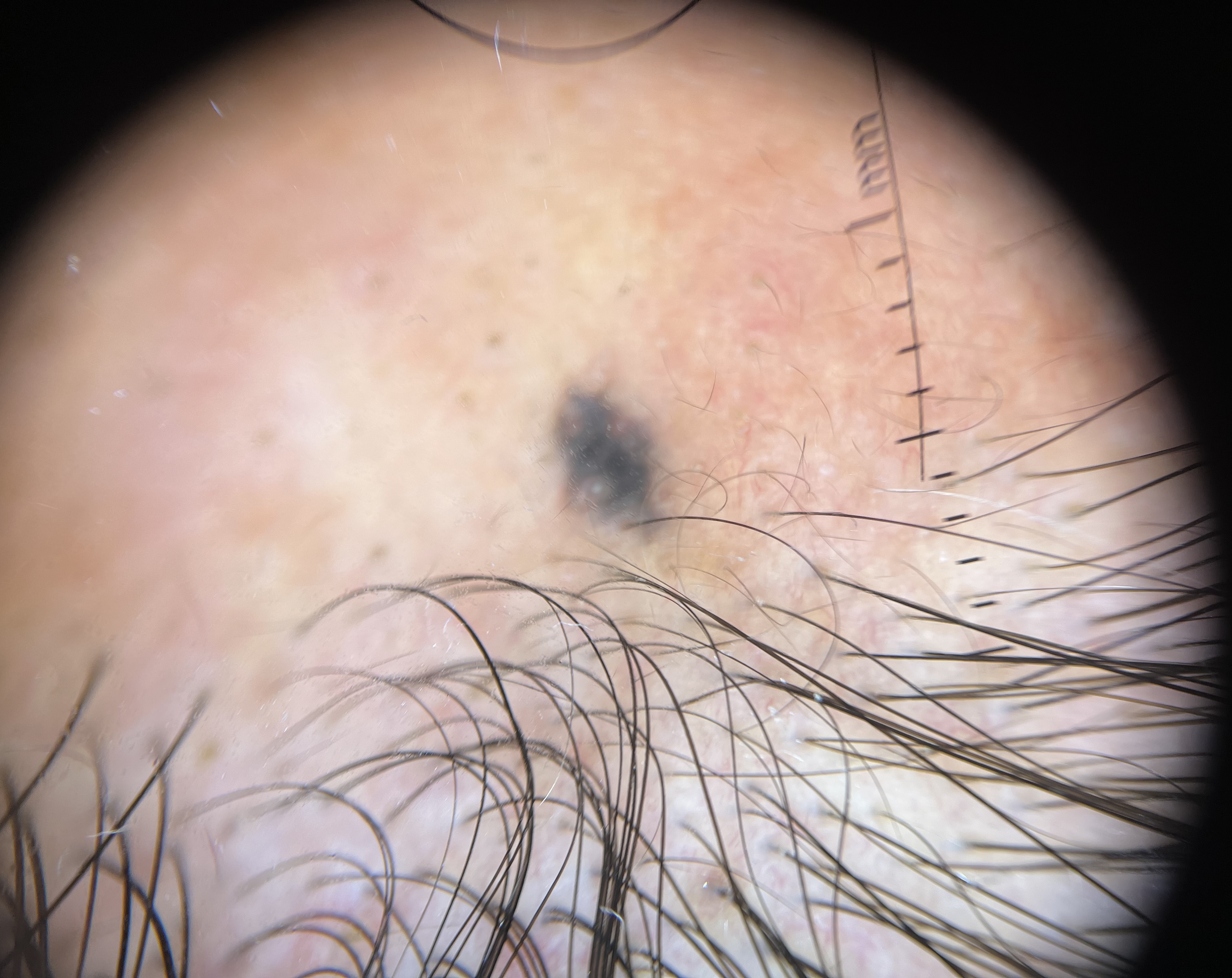image=dermoscopy; subtype=dermal, banal; assessment=blue nevus (expert consensus).